A dermoscopic image of a skin lesion.
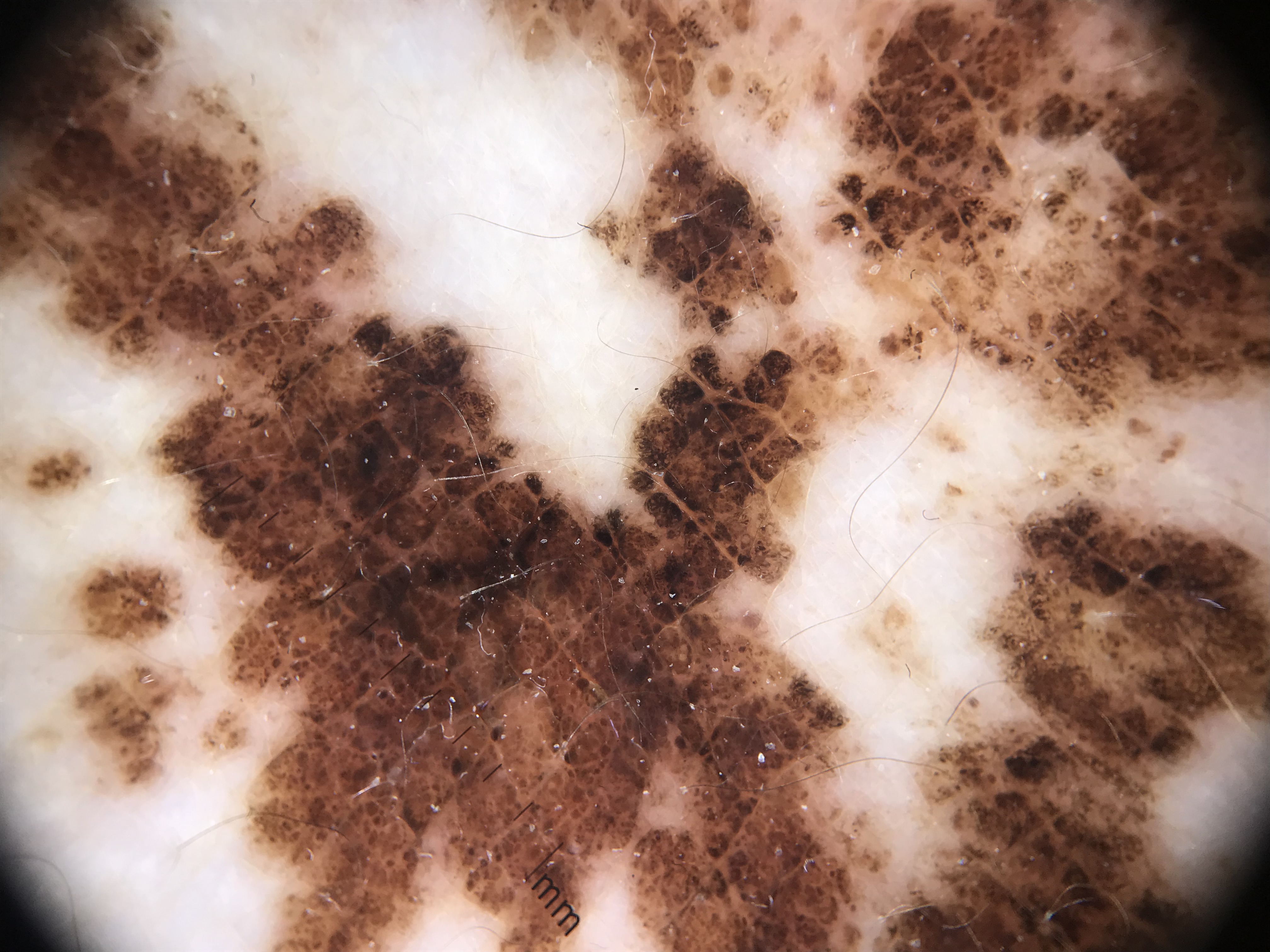label = congenital junctional nevus (expert consensus).